The lesion is described as raised or bumpy, reported duration is less than one week, this is a close-up image, located on the leg, no relevant systemic symptoms.
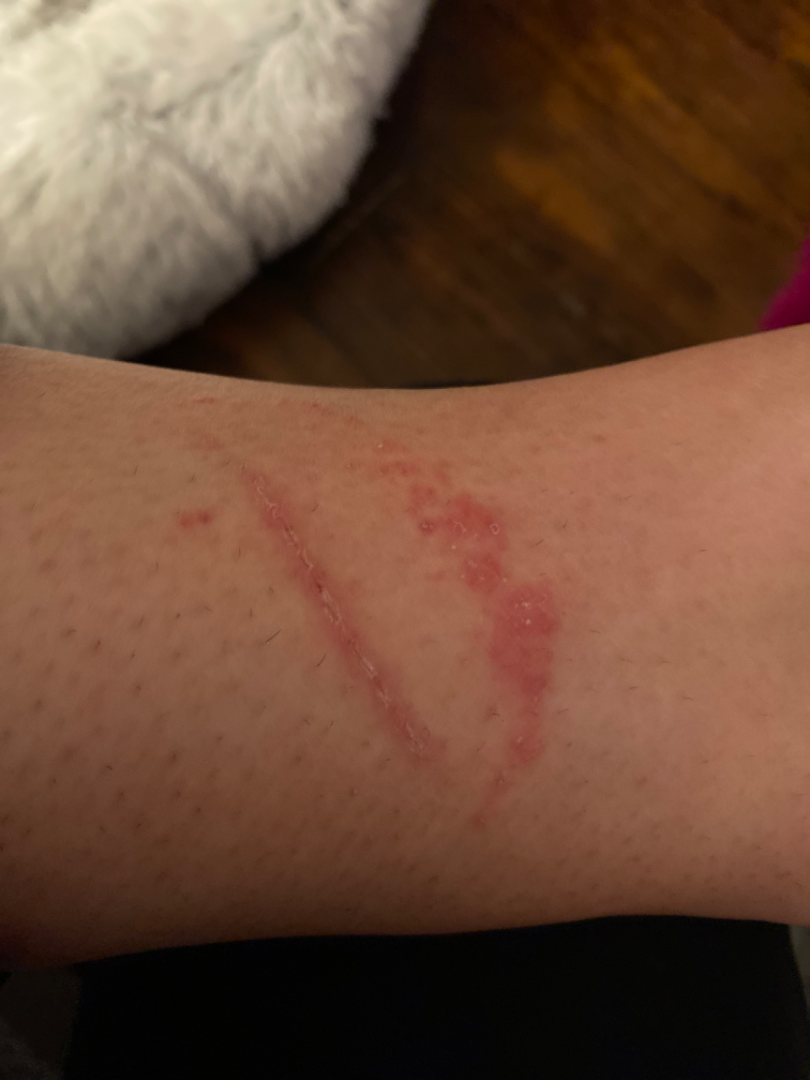diagnostic considerations: Allergic Contact Dermatitis (favored).